A male subject in their 50s · history notes alcohol use, pesticide exposure, prior skin cancer (patient or family), and prior malignancy (patient or family) · the patient was assessed as Fitzpatrick skin type III · a clinical photo of a skin lesion taken with a smartphone.
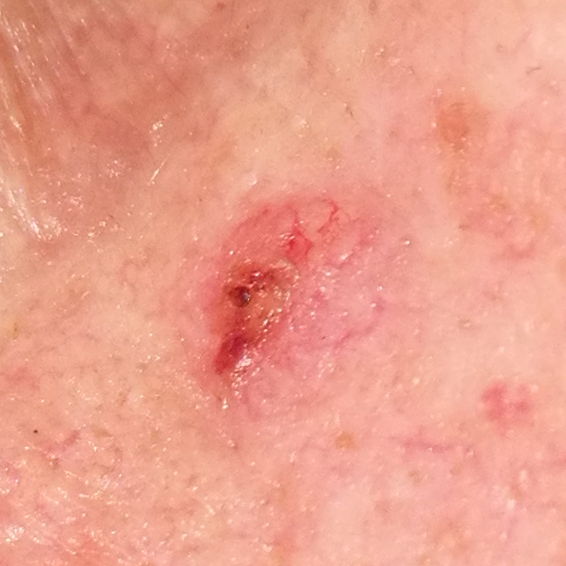Q: Where on the body is the lesion?
A: the face
Q: Lesion size?
A: 4x3 mm
Q: What is this lesion?
A: basal cell carcinoma (biopsy-proven)